The patient reports burning, pain and darkening; texture is reported as raised or bumpy and rough or flaky; located on the leg; no associated systemic symptoms reported; a close-up photograph; the subject is 30–39, male — 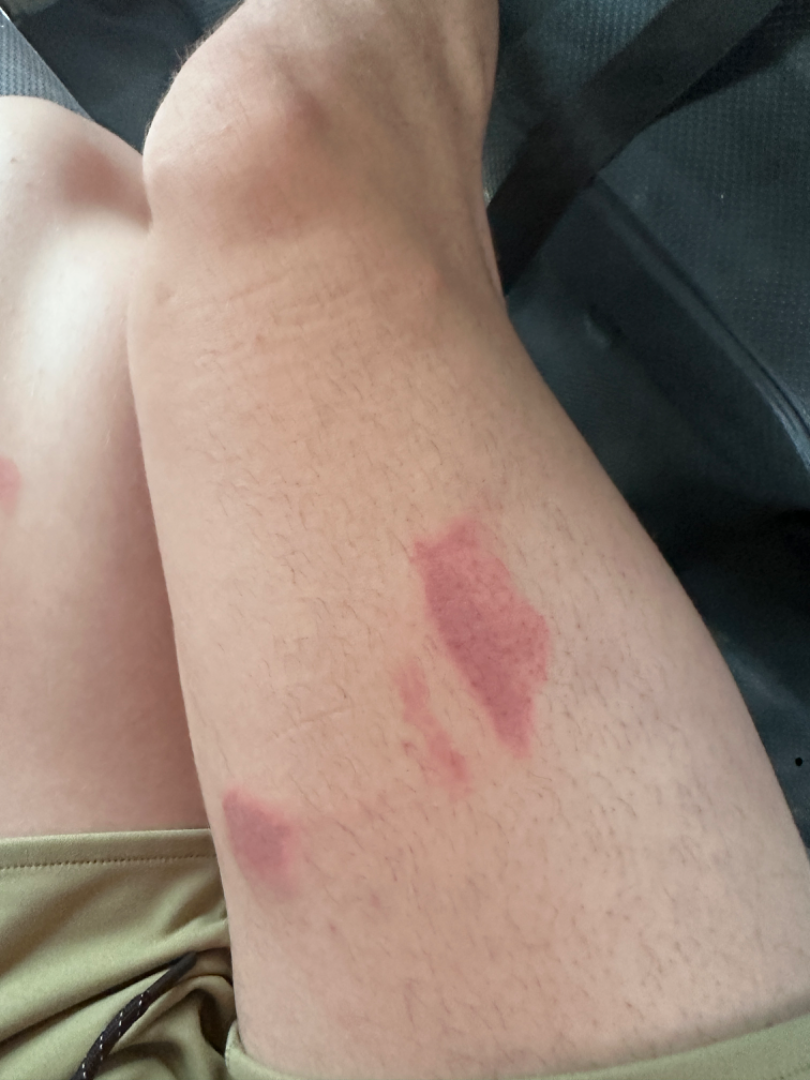On teledermatology review: Abrasion and/or friction burn of thigh without infection and Irritant Contact Dermatitis were each considered, in no particular order; less likely is Burn of skin; a more distant consideration is ecchymoses; less probable is Allergic Contact Dermatitis.